A skin lesion imaged with a dermatoscope.
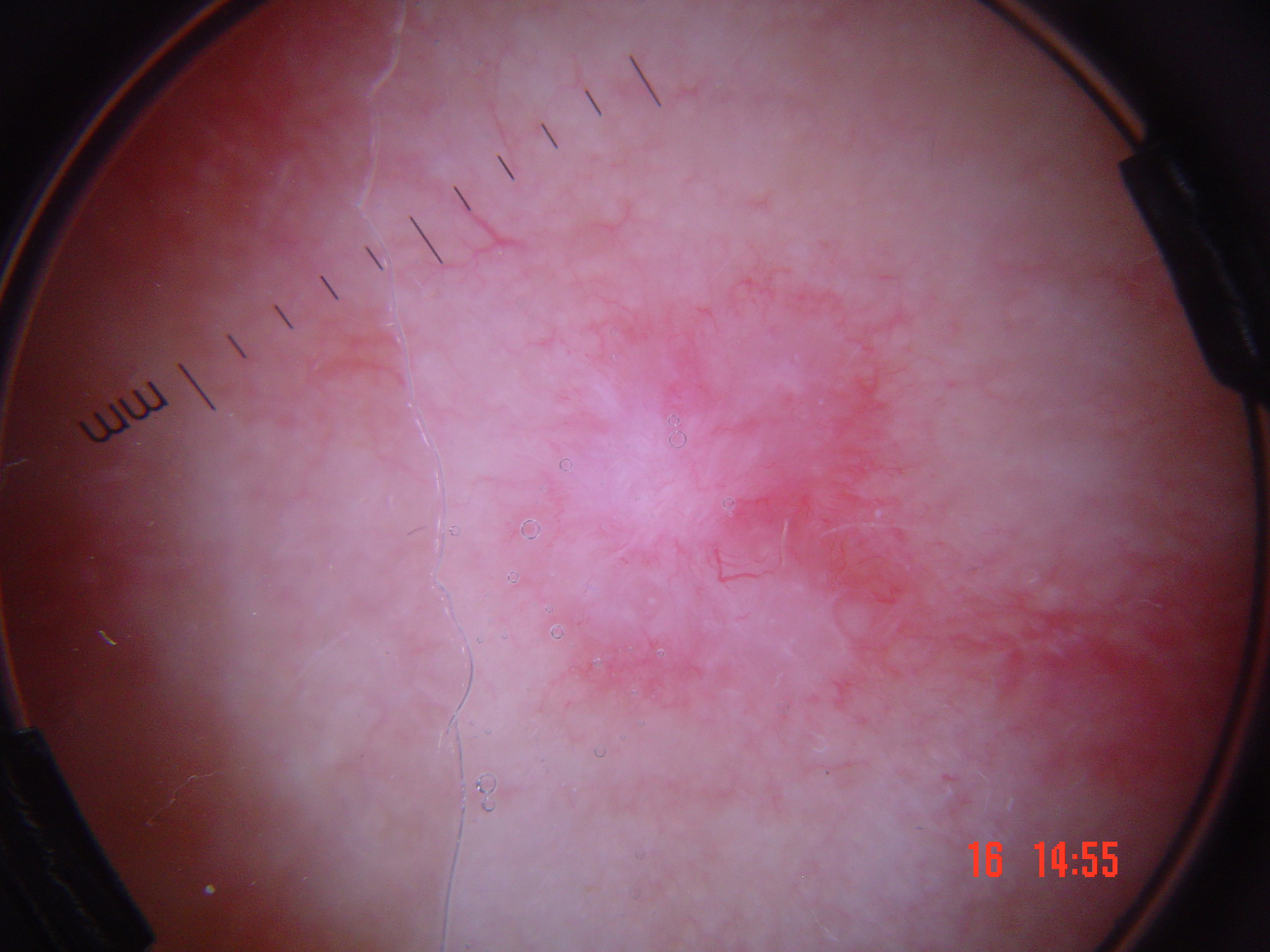diagnosis: squamous cell carcinoma (biopsy-proven)